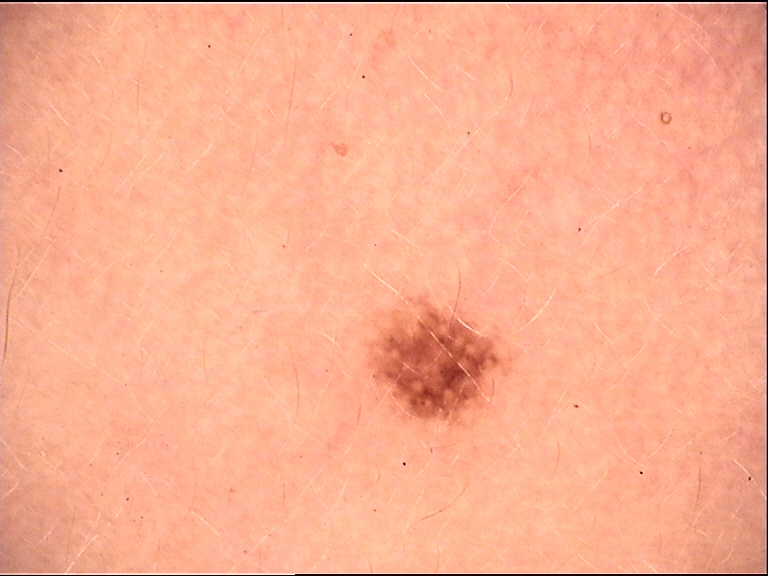Consistent with a compound lesion — a Miescher nevus.